Dermoscopy of a skin lesion.
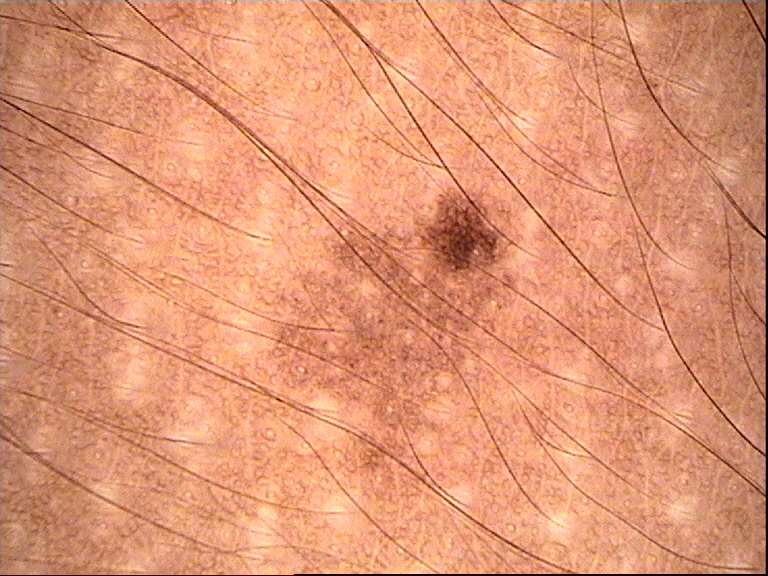label: dysplastic junctional nevus (expert consensus).